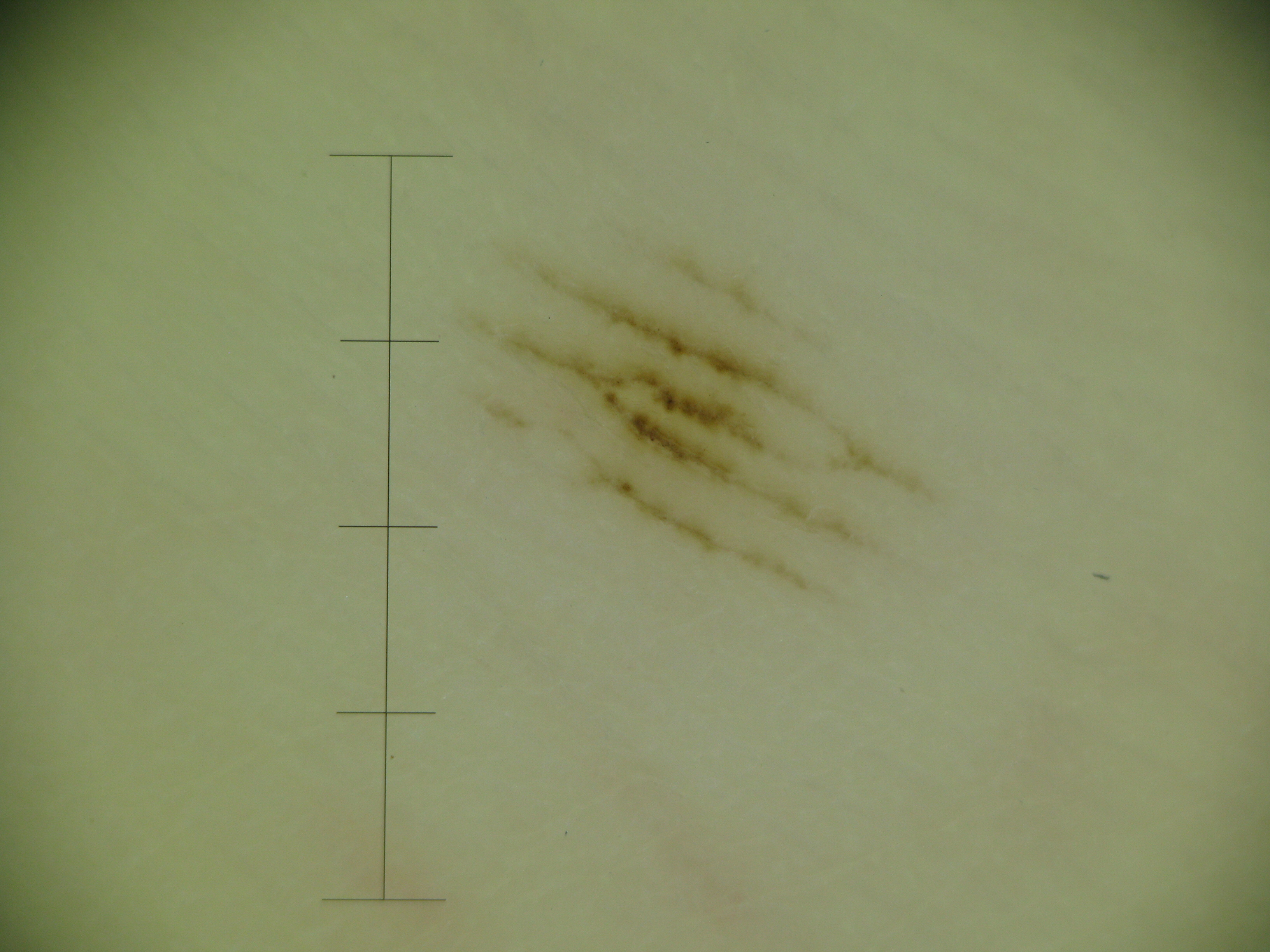image type: dermatoscopy; class: acral junctional nevus (expert consensus).